Located on the arm, close-up view.
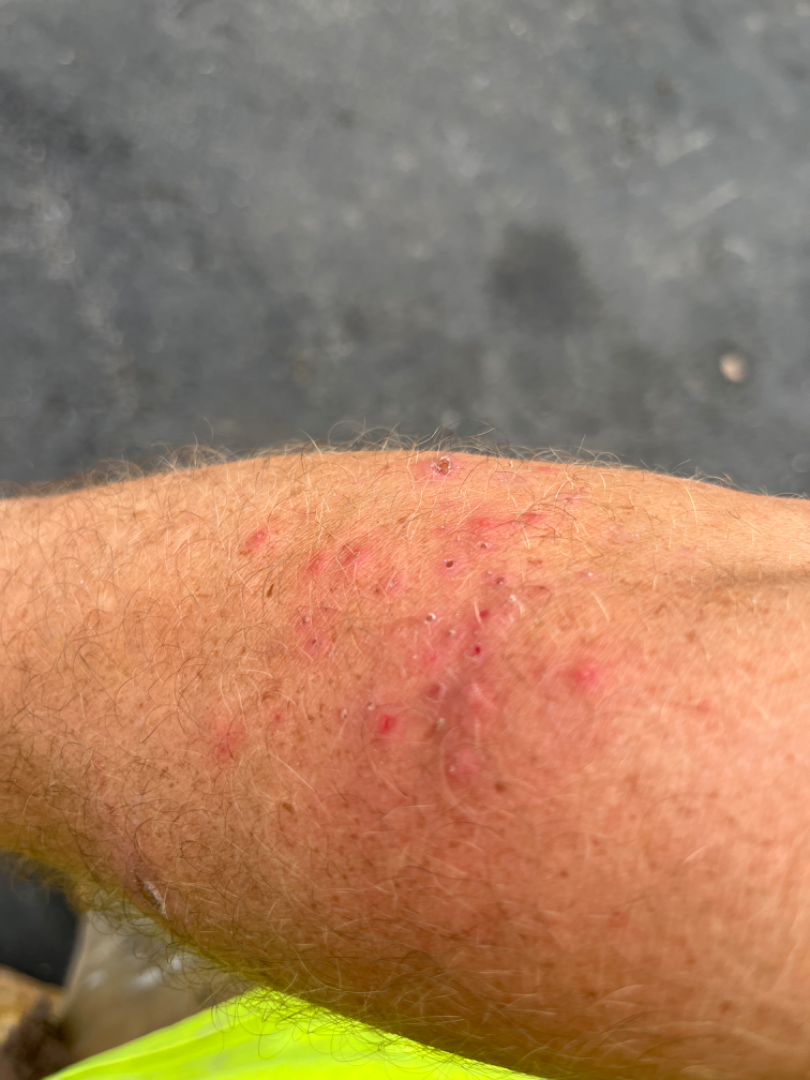On teledermatology review, the leading consideration is Folliculitis; possibly Dermatitis herpetiformis; the differential also includes Acute and chronic dermatitis.